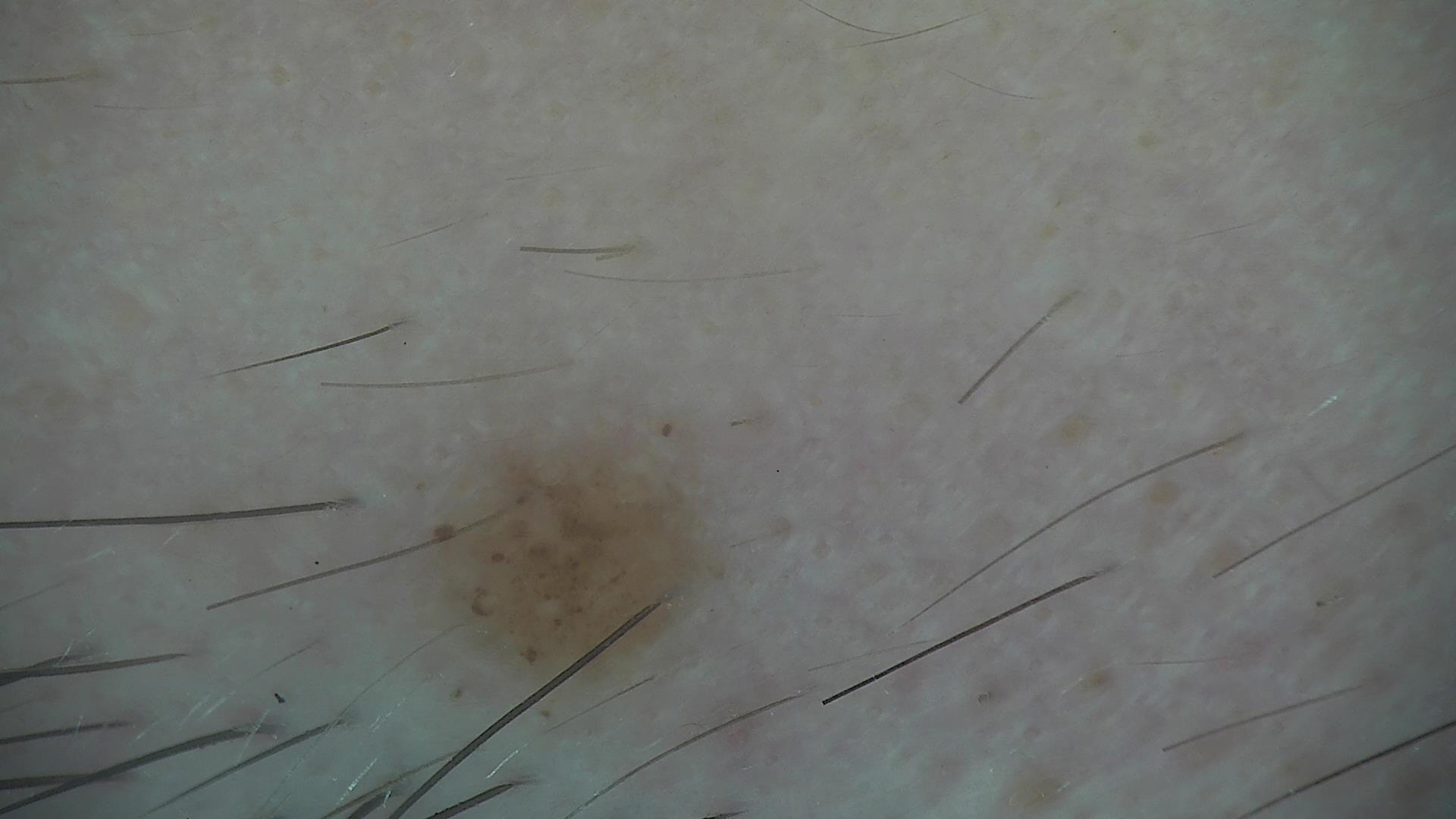A dermoscopic close-up of a skin lesion. Classified as a benign lesion — a dysplastic junctional nevus.